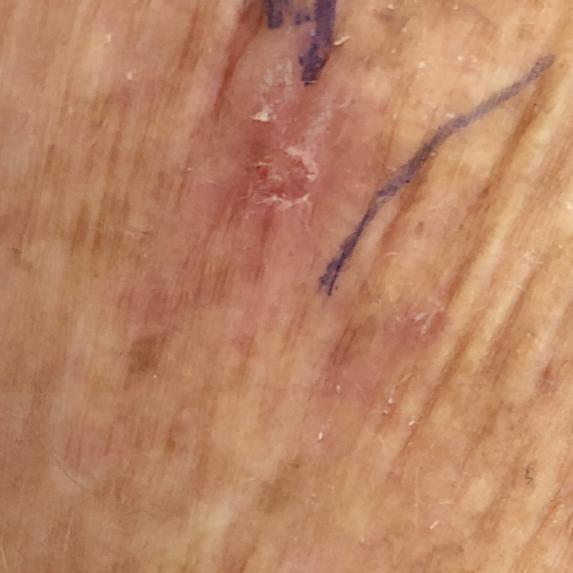image: clinical photo; FST: III; patient: female, in their 70s; size: approx. 11 × 6 mm; diagnosis: actinic keratosis (clinical consensus).